The patient describes having few moles overall. The patient says their skin tans without first burning. Imaged for a research study, with no referral diagnosis recorded. A male patient 67 years of age: 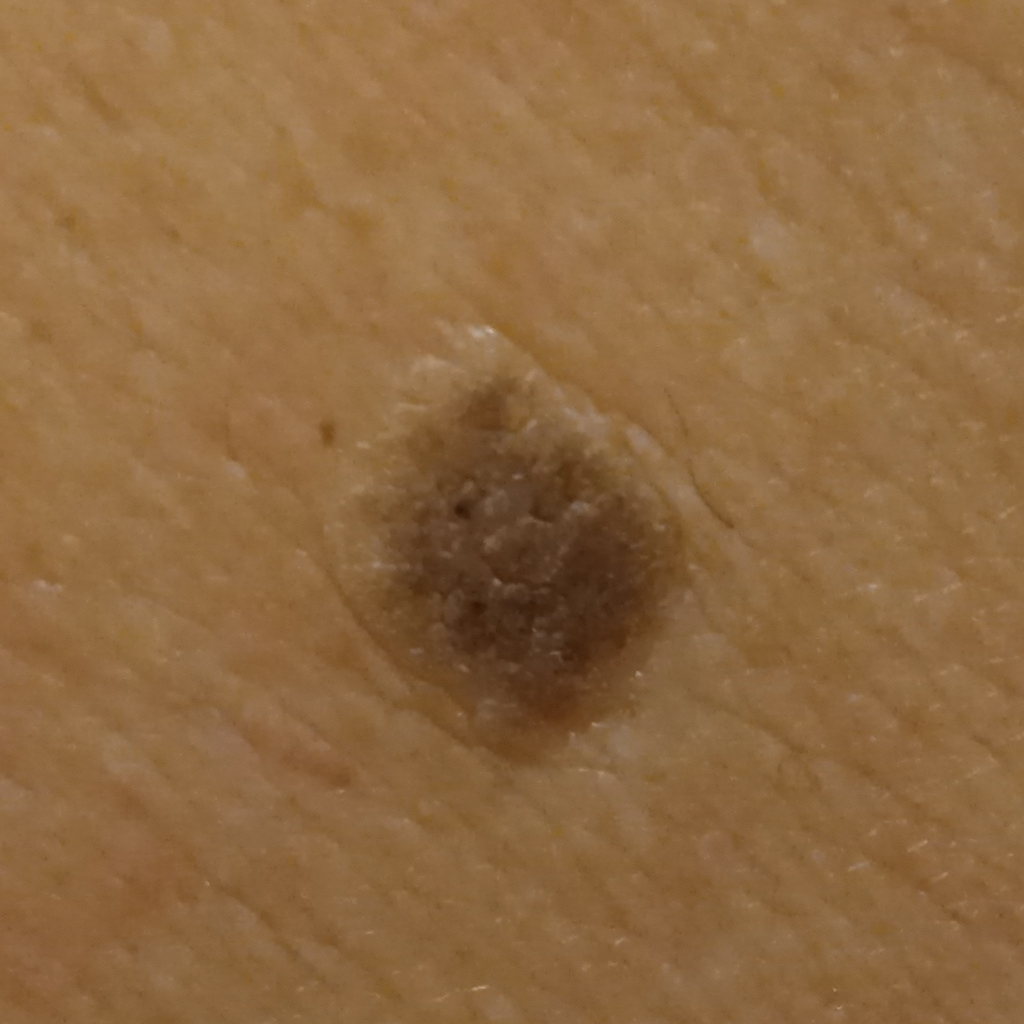Q: Where is the lesion?
A: the back
Q: How large is the lesion?
A: 8.9 mm
Q: What was the diagnosis?
A: seborrheic keratosis (dermatologist consensus)